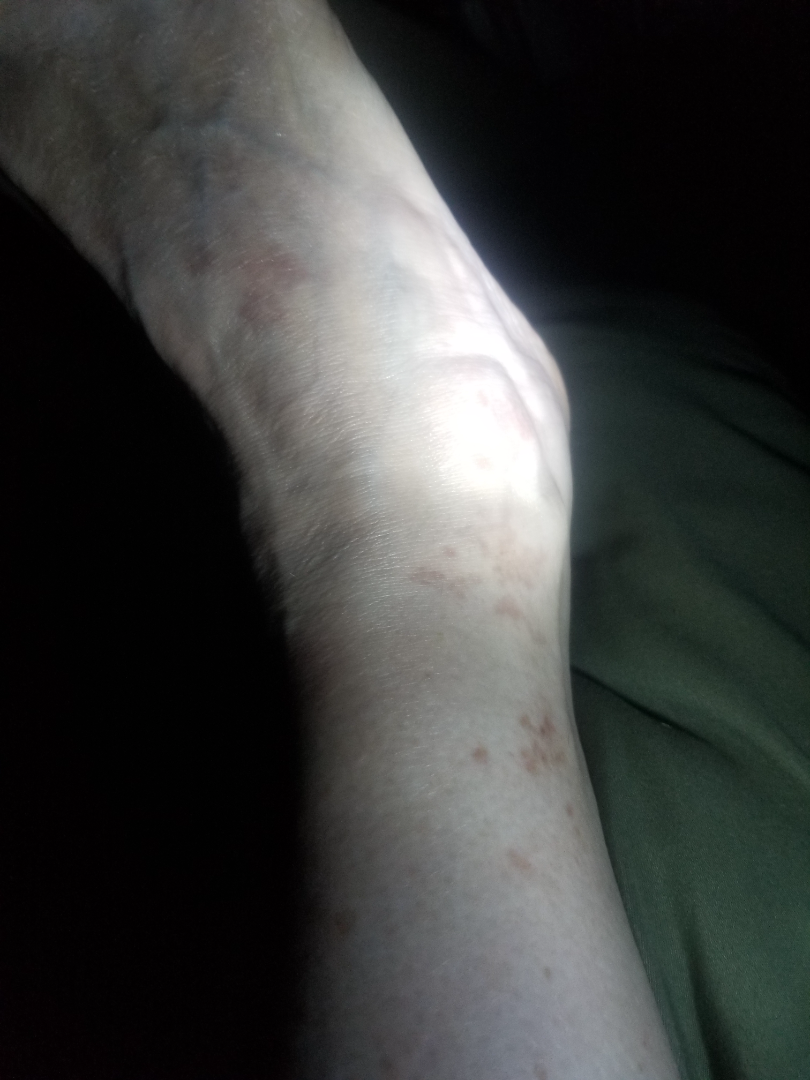The skin findings could not be characterized from the image.
The affected area is the top or side of the foot.
A close-up photograph.
The subject is 60–69, female.
Reported duration is three to twelve months.
Associated systemic symptoms include fatigue, joint pain, mouth sores and shortness of breath.
Symptoms reported: pain, darkening and enlargement.